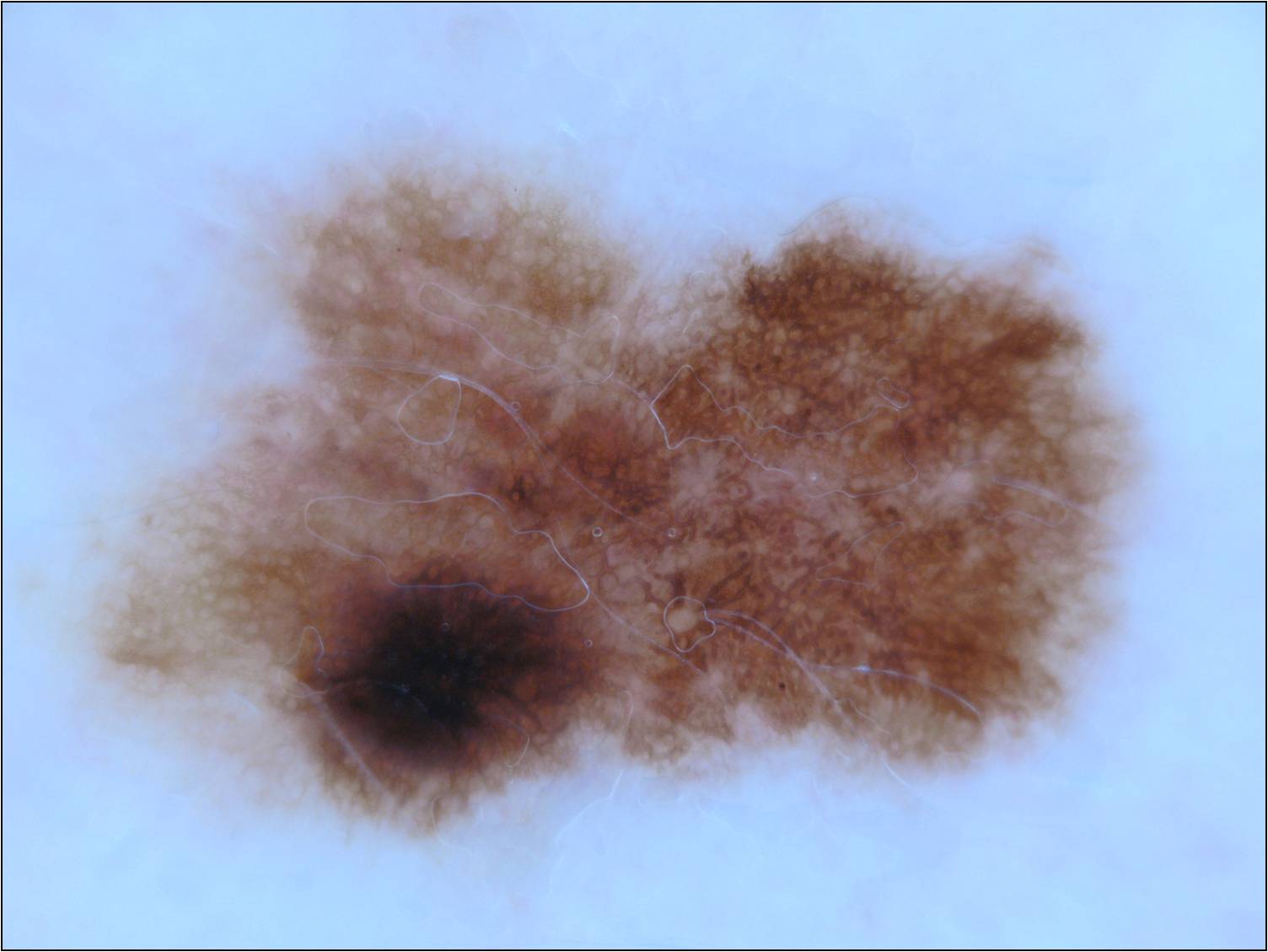{
  "image": {
    "modality": "dermoscopy"
  },
  "lesion_location": {
    "bbox_xyxy": [
      13,
      114,
      1163,
      888
    ]
  },
  "lesion_extent": {
    "approx_field_fraction_pct": 52
  },
  "dermoscopic_features": {
    "present": [
      "globules",
      "pigment network"
    ],
    "absent": [
      "negative network",
      "milia-like cysts",
      "streaks"
    ]
  },
  "diagnosis": {
    "name": "melanocytic nevus",
    "malignancy": "benign",
    "lineage": "melanocytic",
    "provenance": "clinical"
  }
}